A dermatoscopic image of a skin lesion:
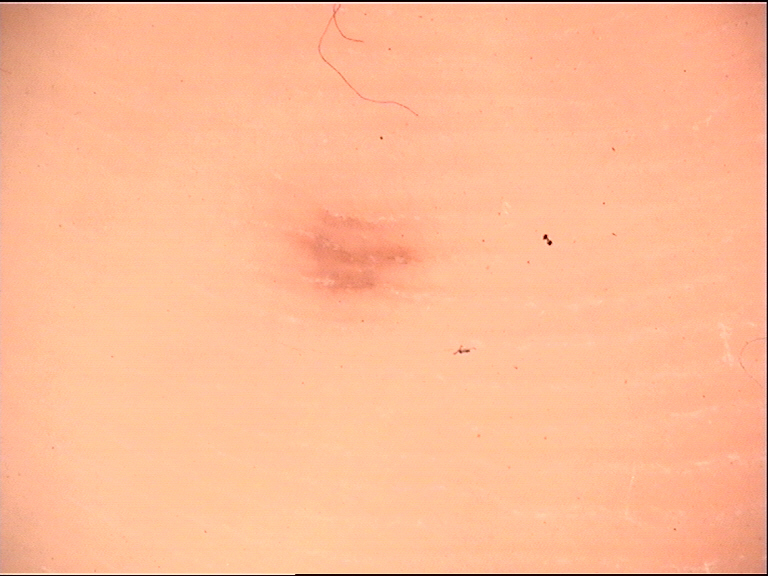Case:
– label · acral dysplastic junctional nevus (expert consensus)